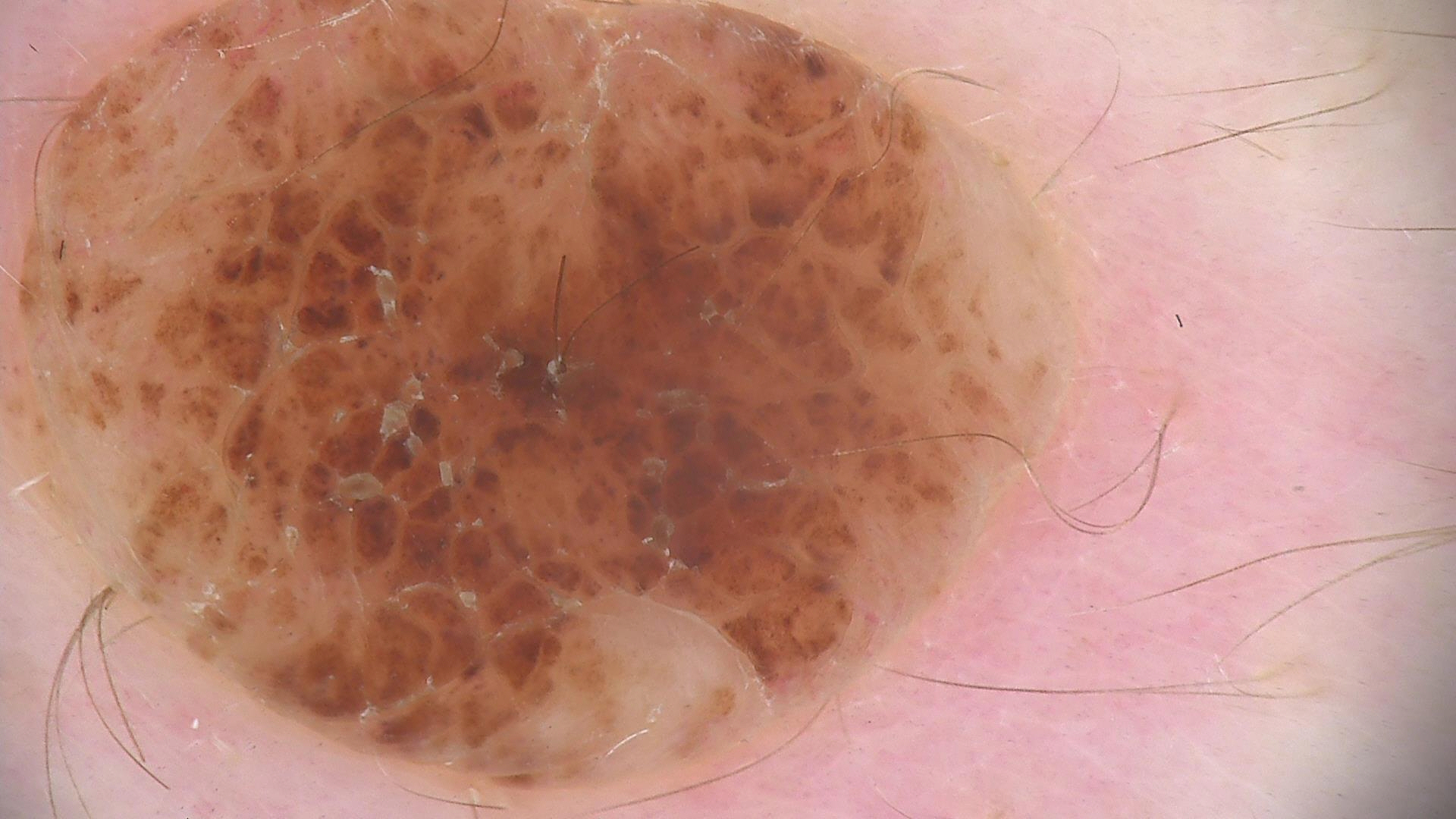Case:
– class · compound nevus (expert consensus)